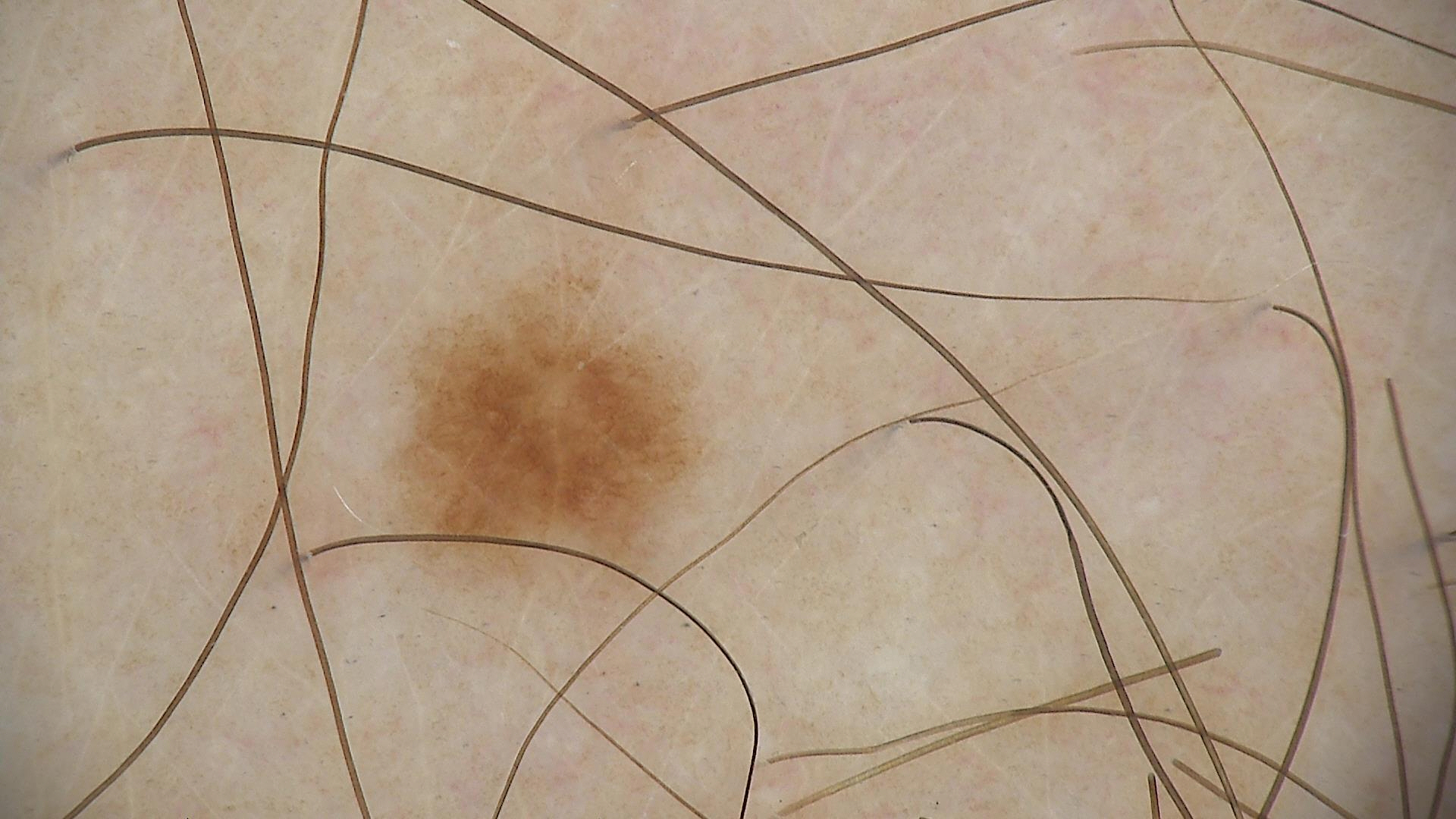A dermoscopic image of a skin lesion. The diagnosis was a banal lesion — a junctional nevus.